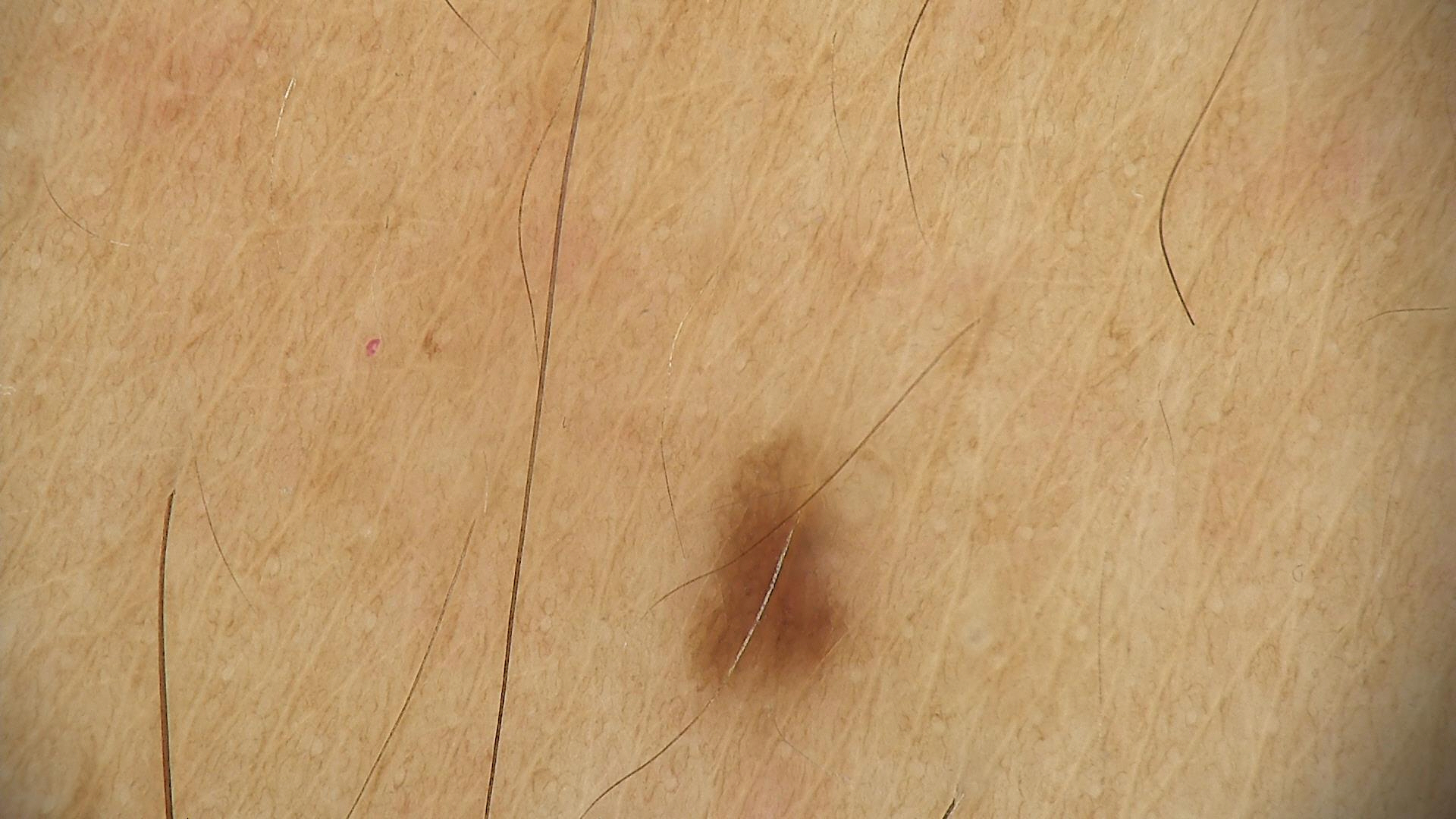Findings:
• assessment — junctional nevus (expert consensus)